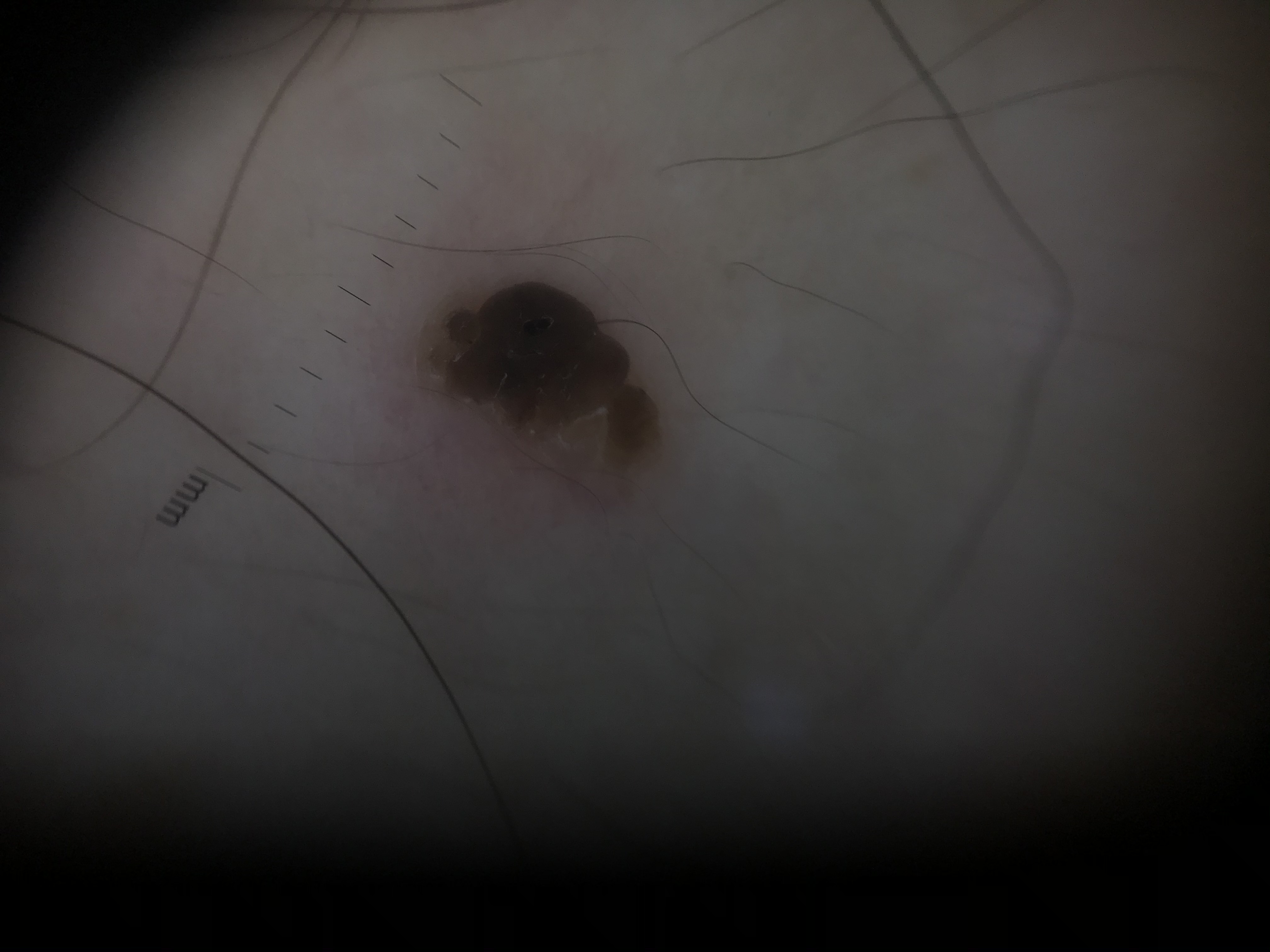Findings:
• diagnostic label — seborrheic keratosis (expert consensus)